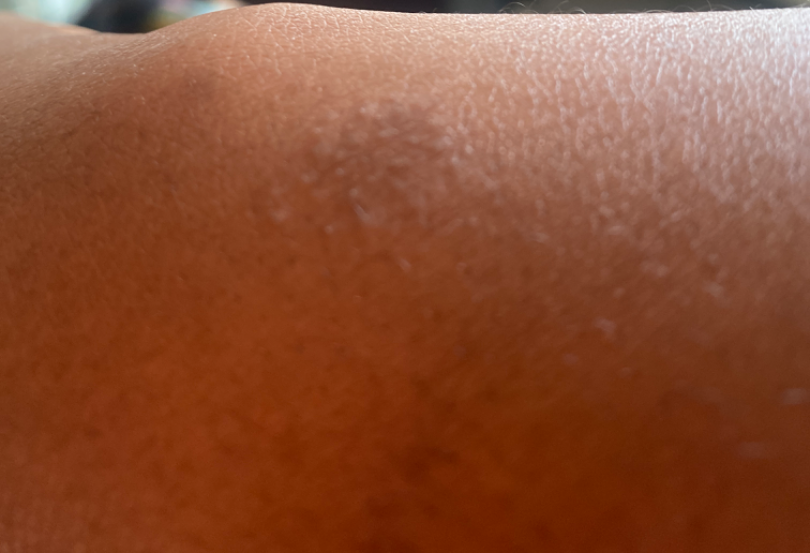The condition could not be reliably identified from the image.
The affected area is the arm.
The photograph was taken at an angle.
The patient reported no systemic symptoms.
Texture is reported as rough or flaky.
The contributor reports enlargement and bothersome appearance.
The condition has been present for one to four weeks.